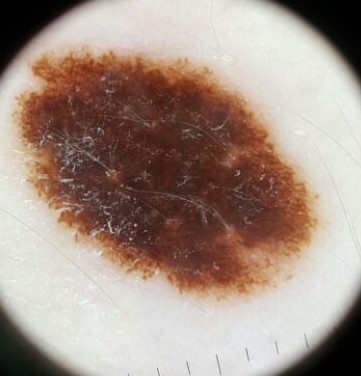Findings:
Dermoscopy of a skin lesion.
Impression:
Labeled as a dysplastic compound nevus.